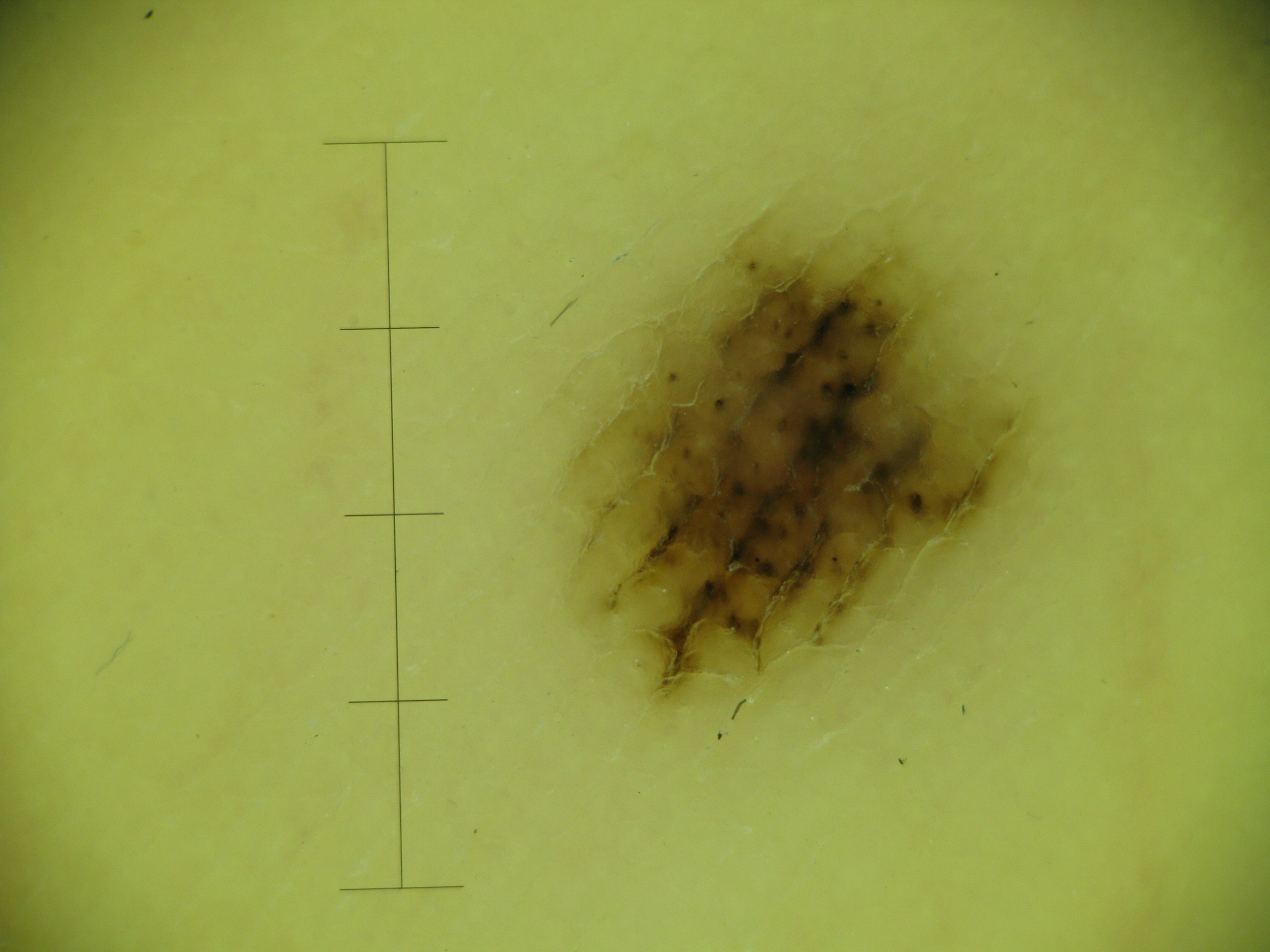<dermoscopy>
<diagnosis>
<name>acral compound nevus</name>
<code>acb</code>
<malignancy>benign</malignancy>
<super_class>melanocytic</super_class>
<confirmation>expert consensus</confirmation>
</diagnosis>
</dermoscopy>